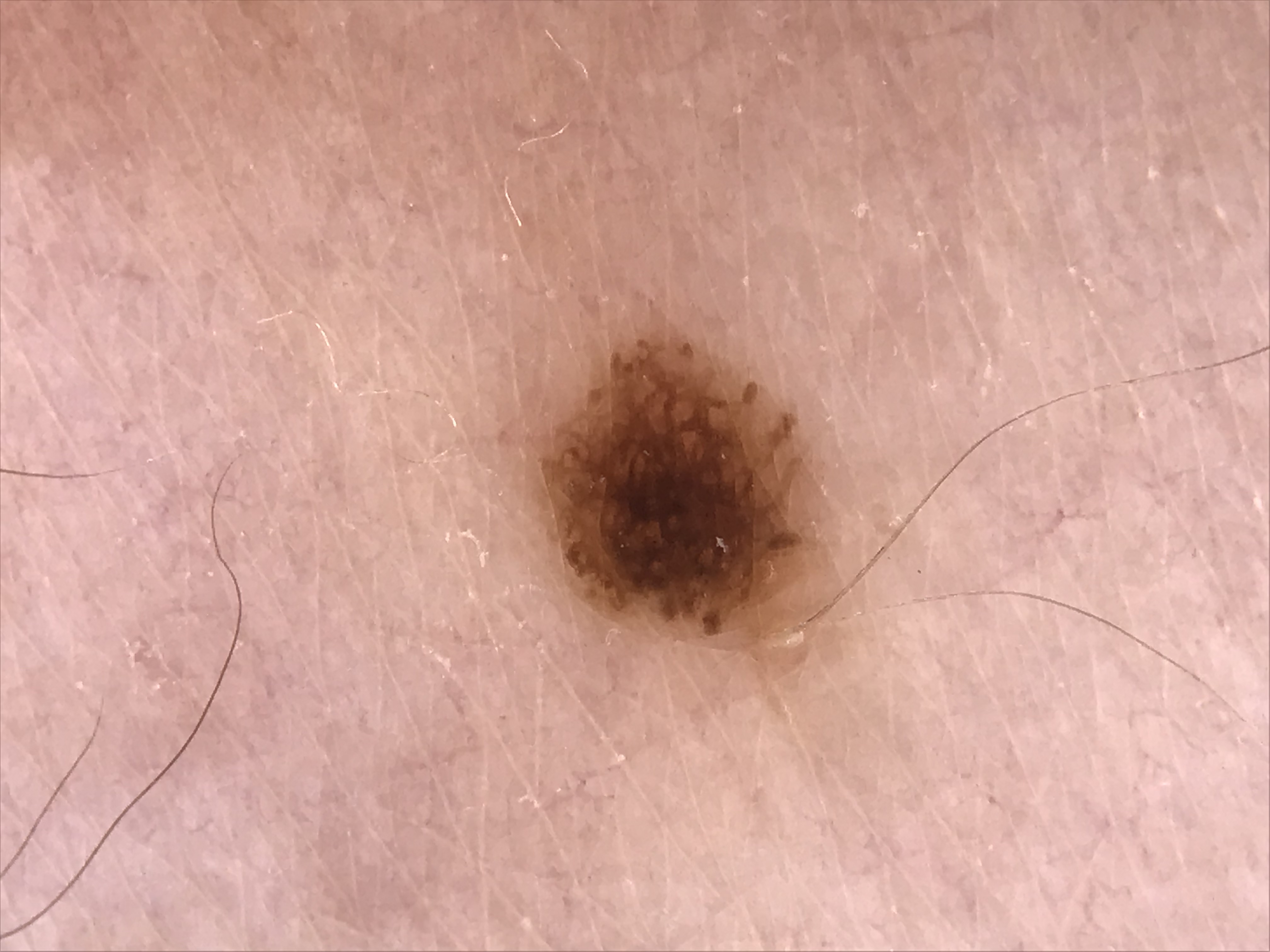class=dysplastic junctional nevus (expert consensus)